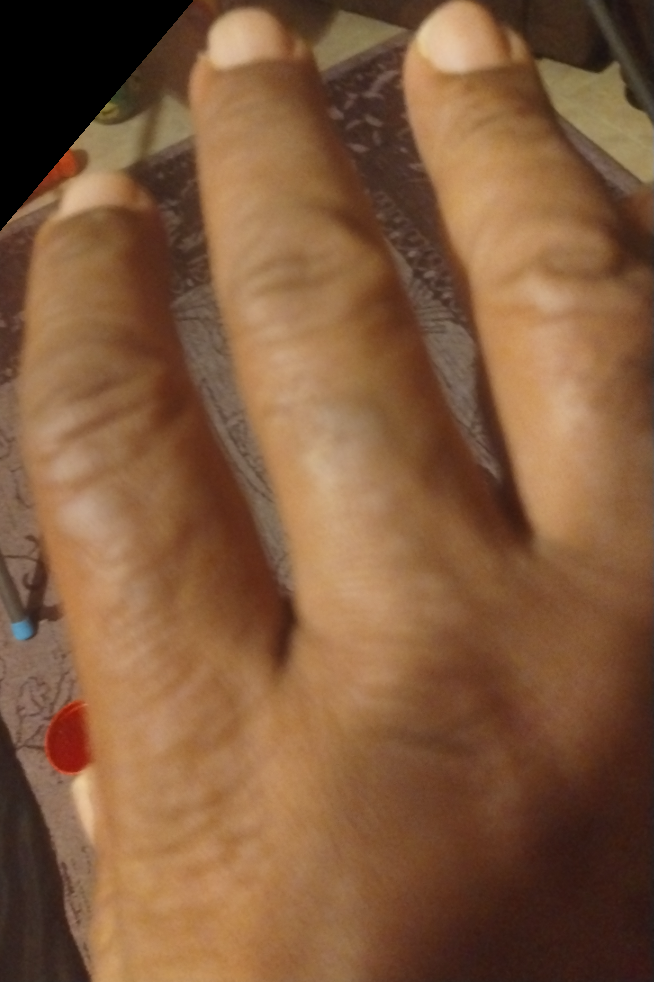Impression:
Diagnostic features were not clearly distinguishable in this photograph.
History:
The photograph is a close-up of the affected area. The contributor reports the condition has been present for three to twelve months. The back of the hand is involved. The lesion is described as raised or bumpy. The patient considered this a rash. No associated systemic symptoms reported.